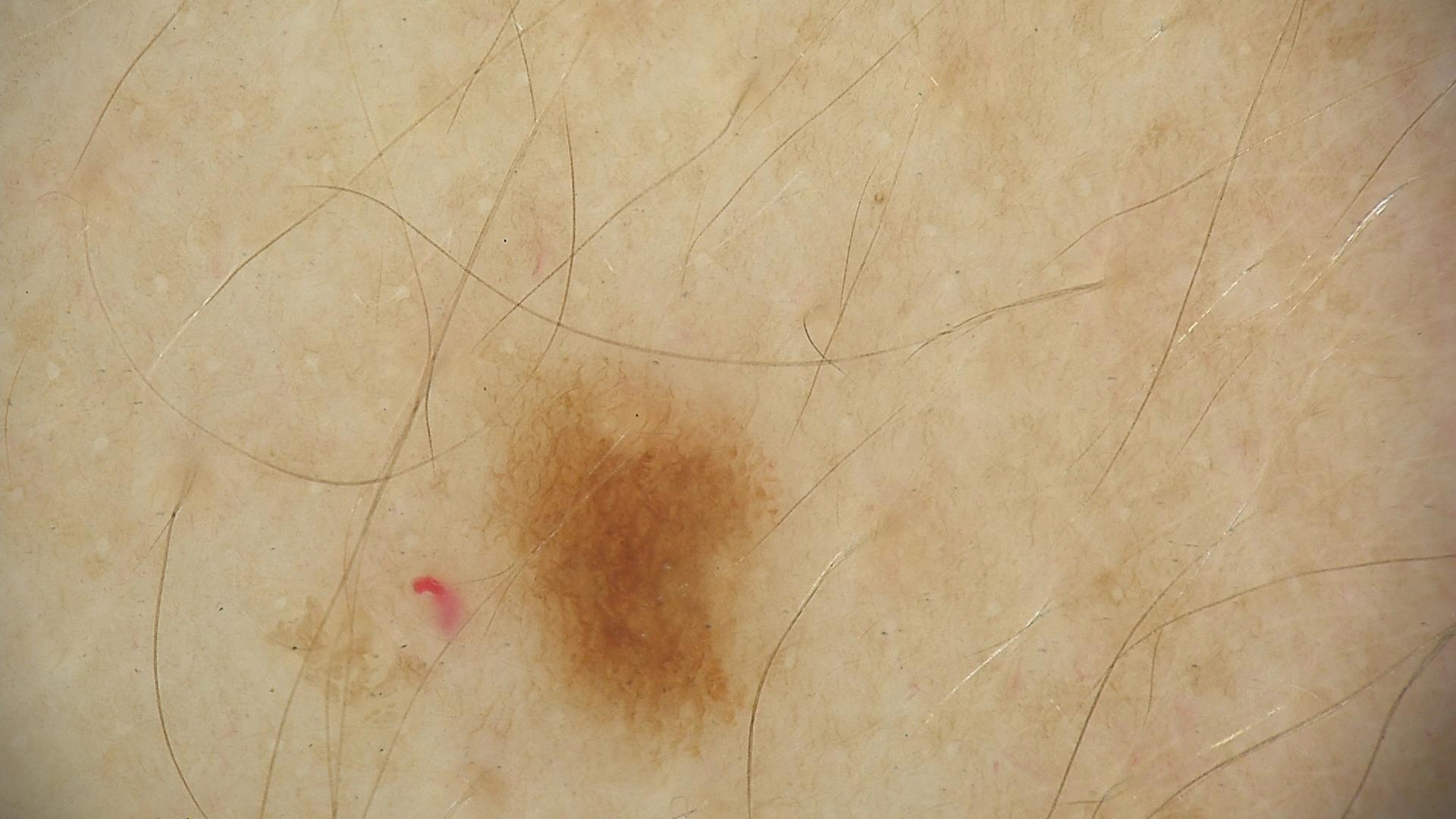label: dysplastic junctional nevus (expert consensus).